Dermoscopy of a skin lesion — 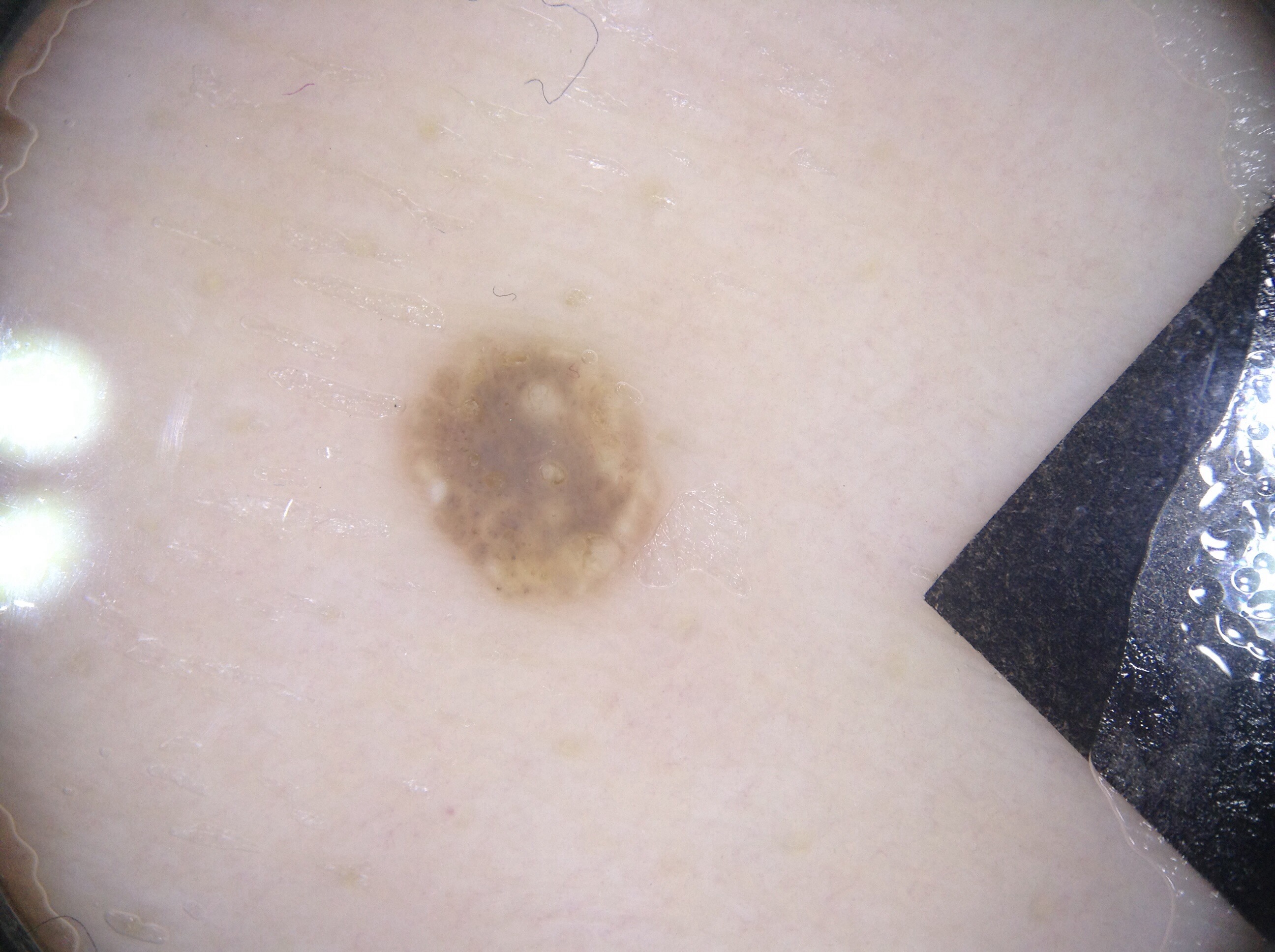Findings:
On dermoscopy, the lesion shows milia-like cysts; no negative network, pigment network, or streaks. The lesion spans x1=386, y1=317, x2=679, y2=618. The lesion takes up about 5% of the image.
Assessment:
Expert review diagnosed this as a seborrheic keratosis, a benign skin lesion.